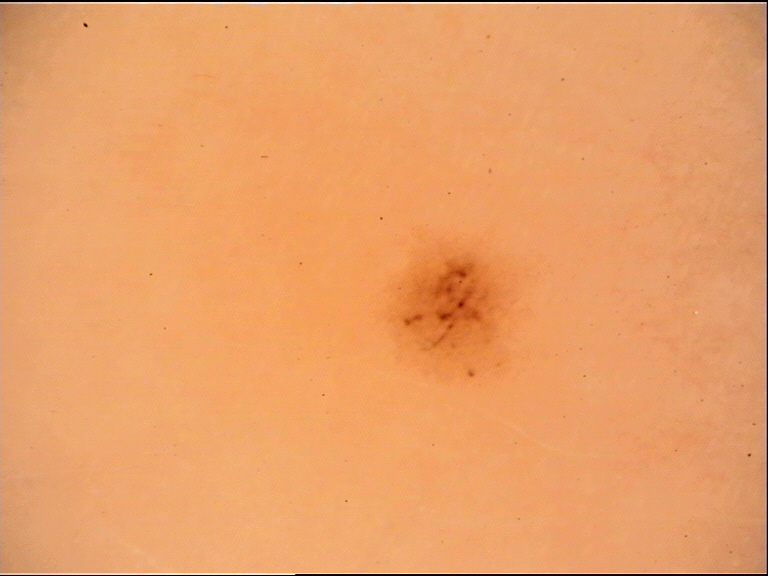Summary:
A dermoscopic close-up of a skin lesion.
Impression:
The diagnostic label was an acral dysplastic junctional nevus.